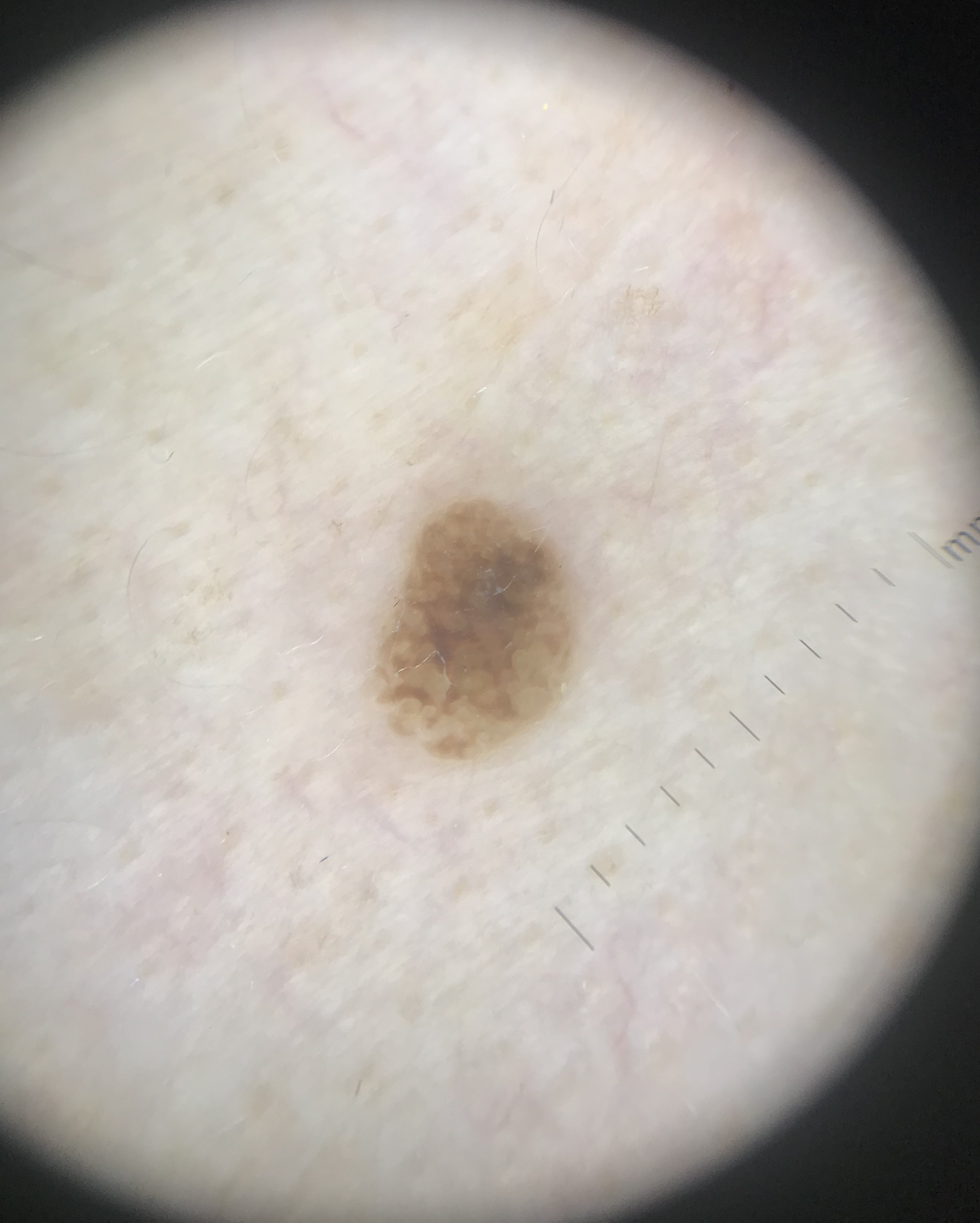Q: What kind of image is this?
A: dermatoscopy
Q: What is this lesion?
A: seborrheic keratosis (expert consensus)